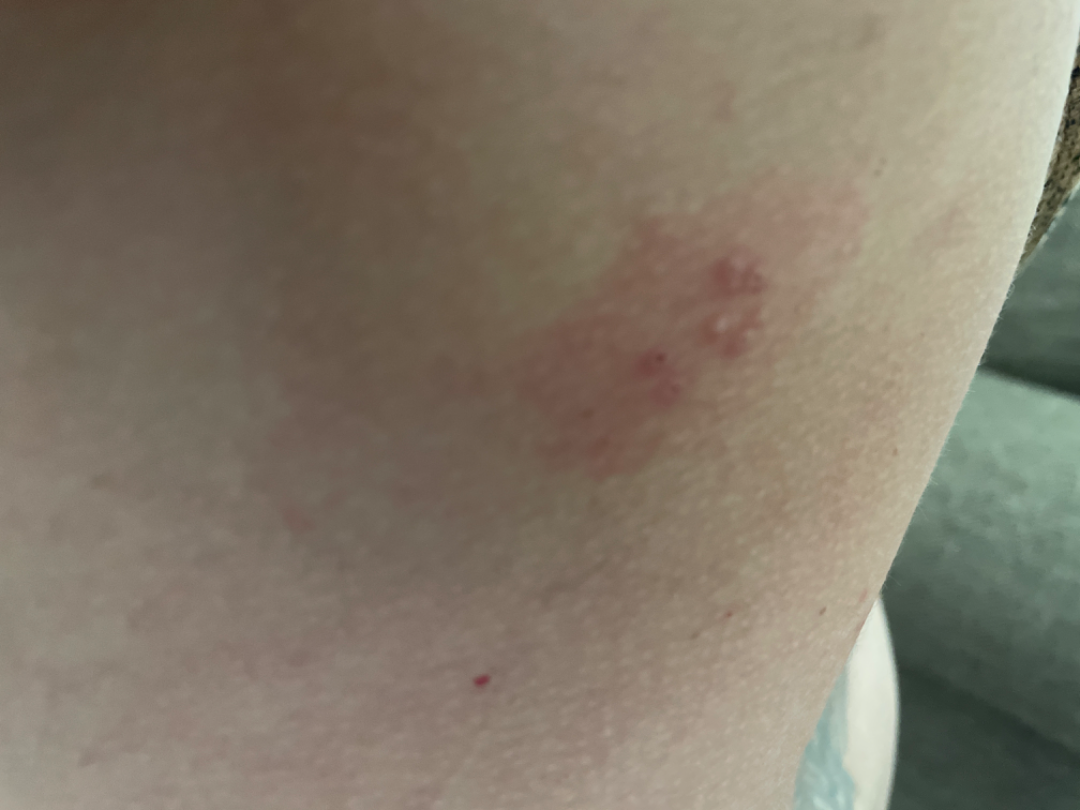The patient notes the lesion is raised or bumpy. Reported duration is less than one week. Reported lesion symptoms include itching, pain and burning. Self-categorized by the patient as skin that appeared healthy to them. The contributor is a female aged 40–49. This is a close-up image. The back of the torso is involved. Three dermatologists independently reviewed the case: most likely Molluscum Contagiosum; also on the differential is Herpes Simplex; a more distant consideration is Impetigo; less likely is Allergic Contact Dermatitis.